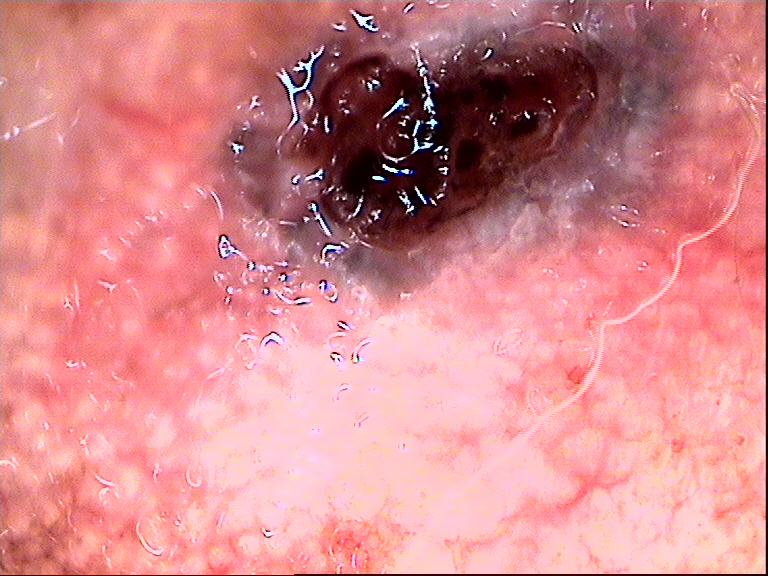The biopsy diagnosis was a basal cell carcinoma.